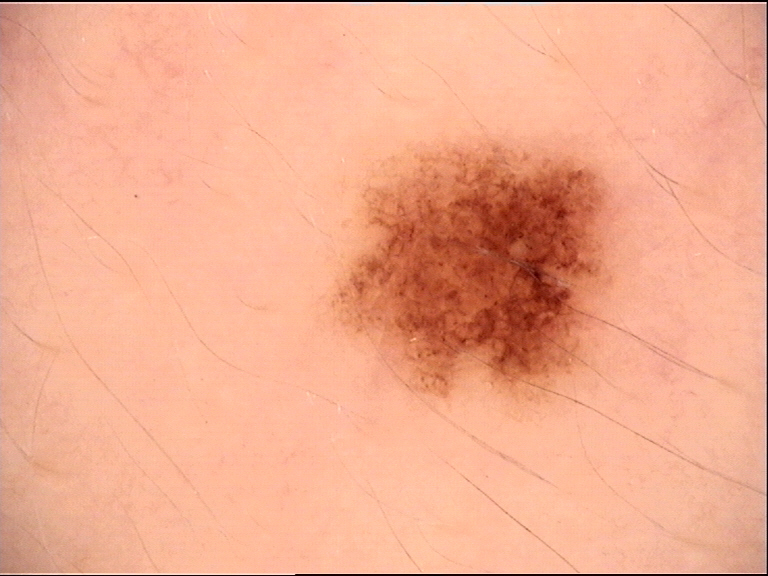Consistent with a dysplastic junctional nevus.